The subject is a male in their mid- to late 60s. A dermoscopic image of a skin lesion — 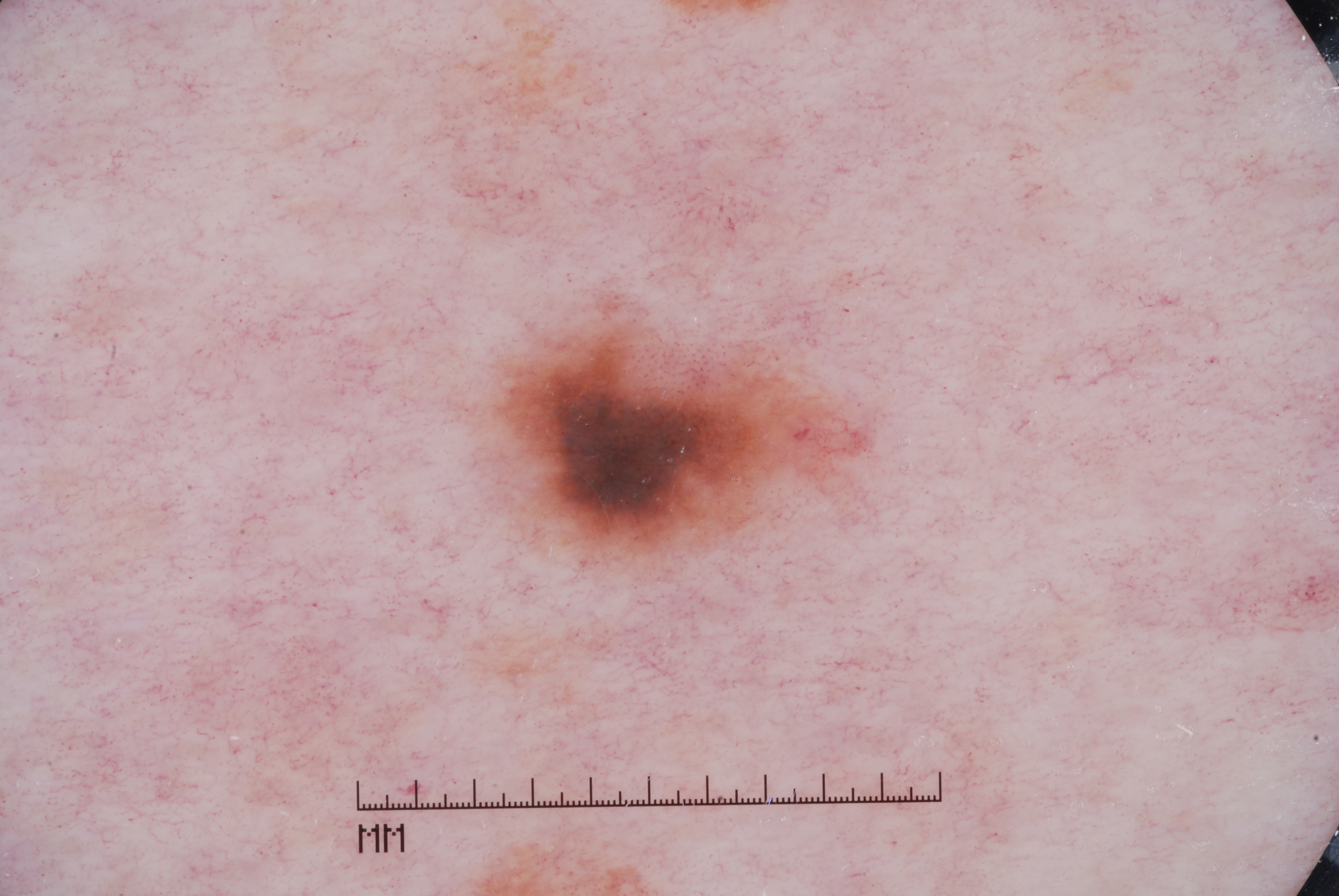Findings:
– dermoscopic findings — pigment network; absent: streaks, negative network, and milia-like cysts
– size — small
– lesion bbox — 491, 309, 868, 567
– impression — a melanocytic nevus